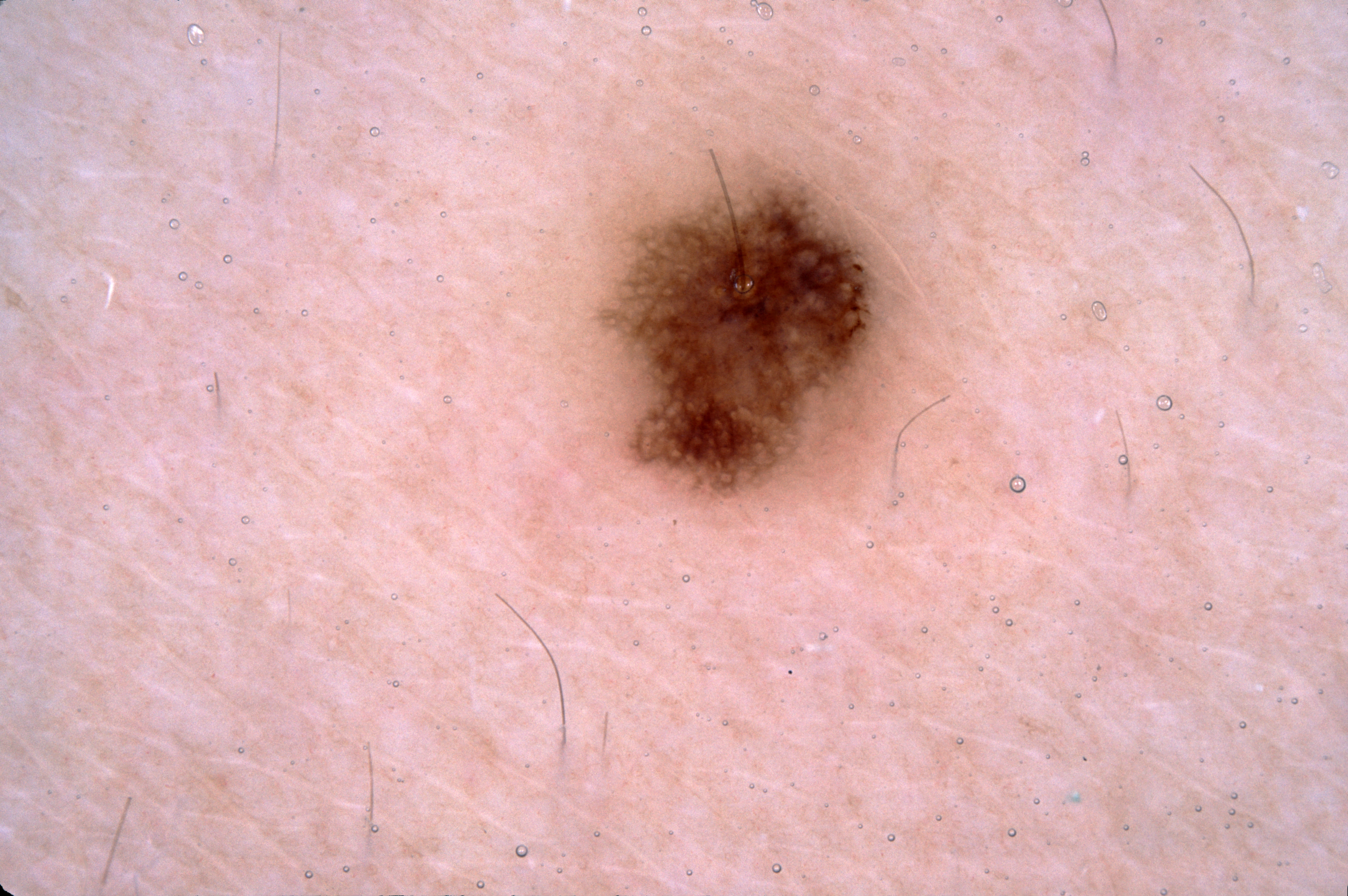Q: How was this image acquired?
A: dermoscopic image
Q: What are the patient's age and sex?
A: female, in their mid- to late 20s
Q: Where is the lesion in the image?
A: bbox(561, 124, 953, 529)
Q: What does dermoscopy show?
A: pigment network; absent: milia-like cysts, streaks, and negative network
Q: Lesion extent?
A: moderate
Q: What is the diagnosis?
A: a melanocytic nevus